A dermoscopic photograph of a skin lesion.
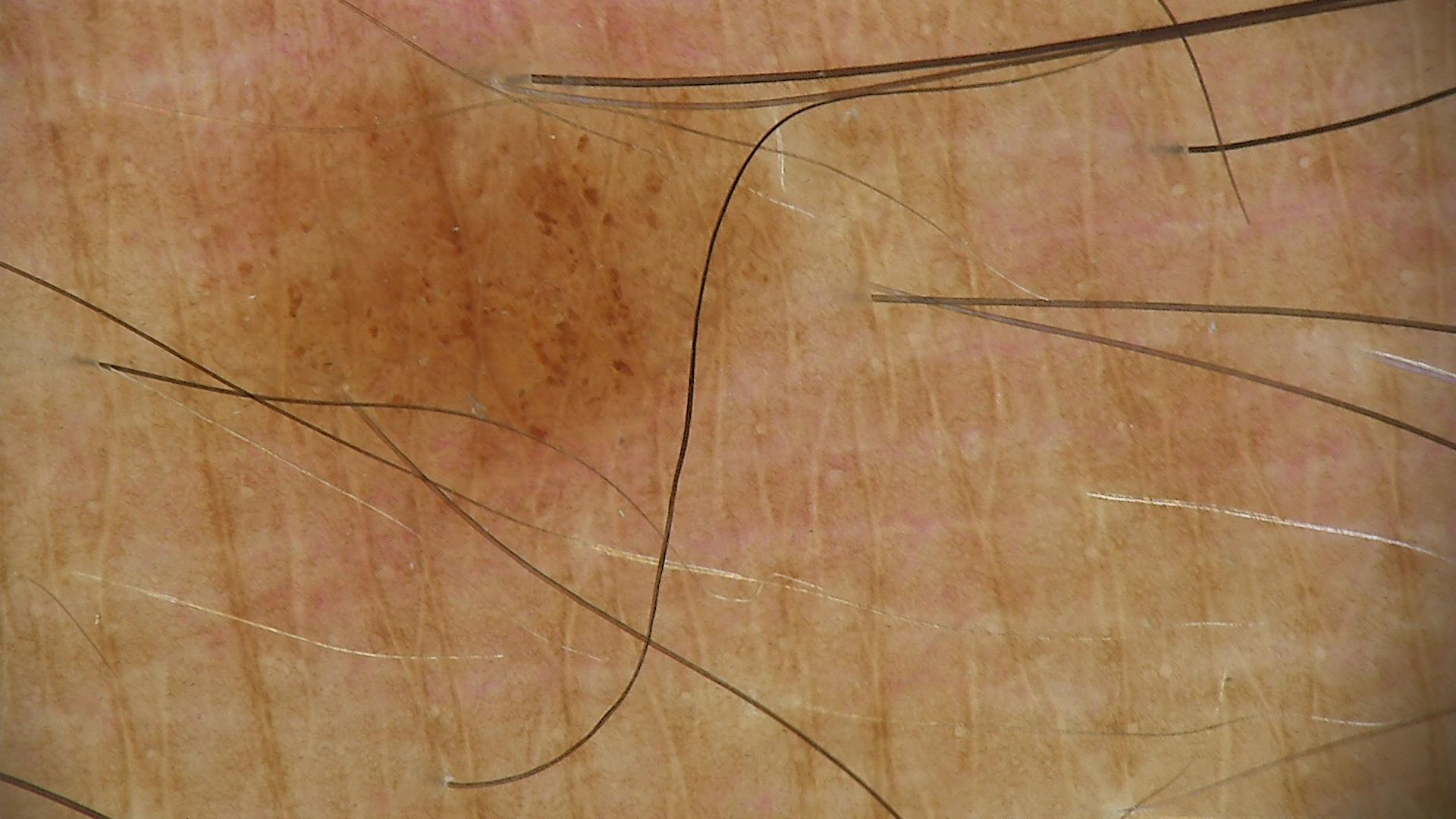The diagnosis was a dysplastic junctional nevus.